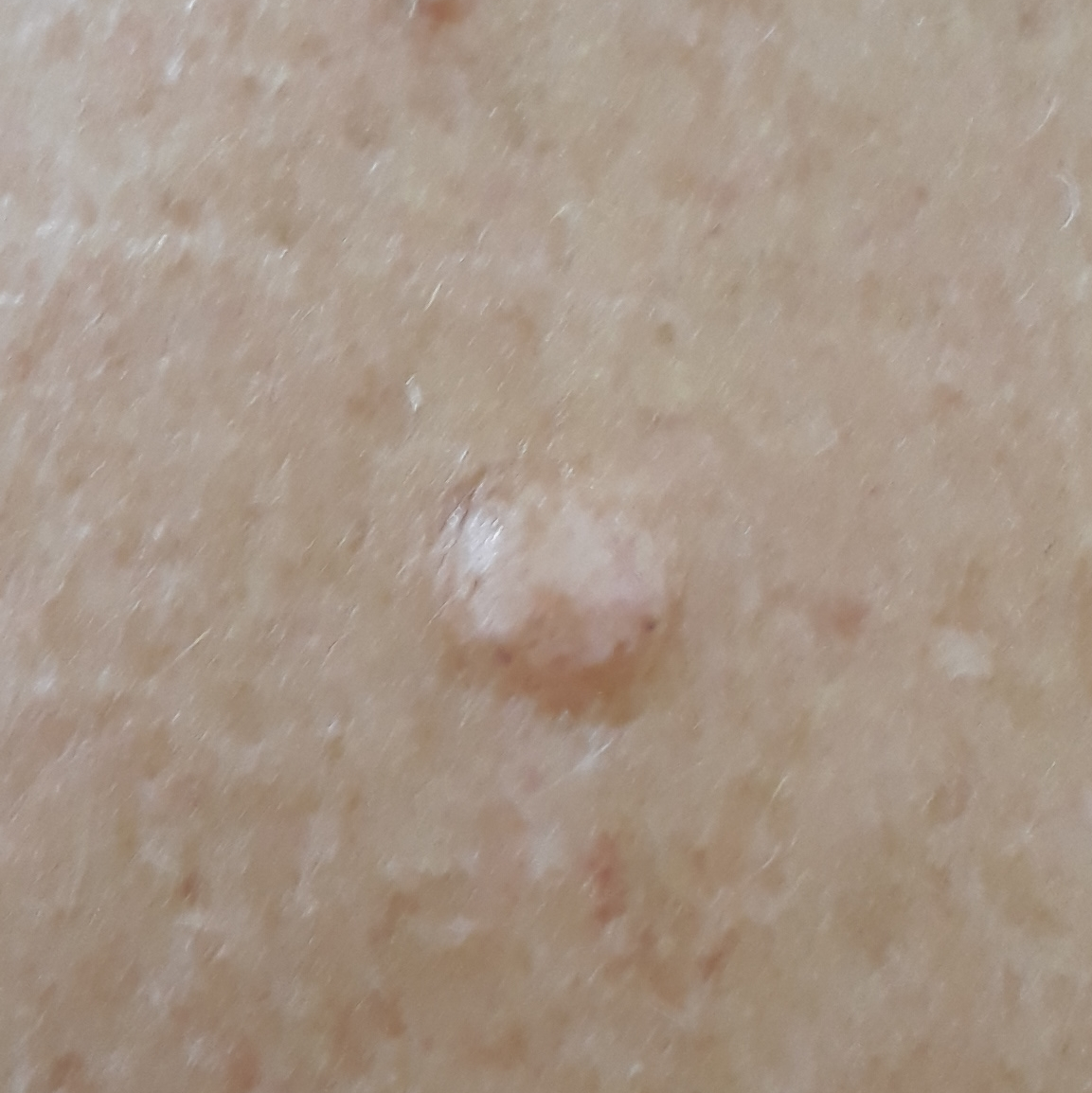Q: Patient demographics?
A: in their late 50s
Q: What kind of image is this?
A: clinical photograph
Q: Where on the body is the lesion?
A: the back
Q: Any reported symptoms?
A: elevation / no pain
Q: What was the clinical impression?
A: nevus (clinical consensus)